A dermoscopy image of a single skin lesion · a male subject, roughly 10 years of age:
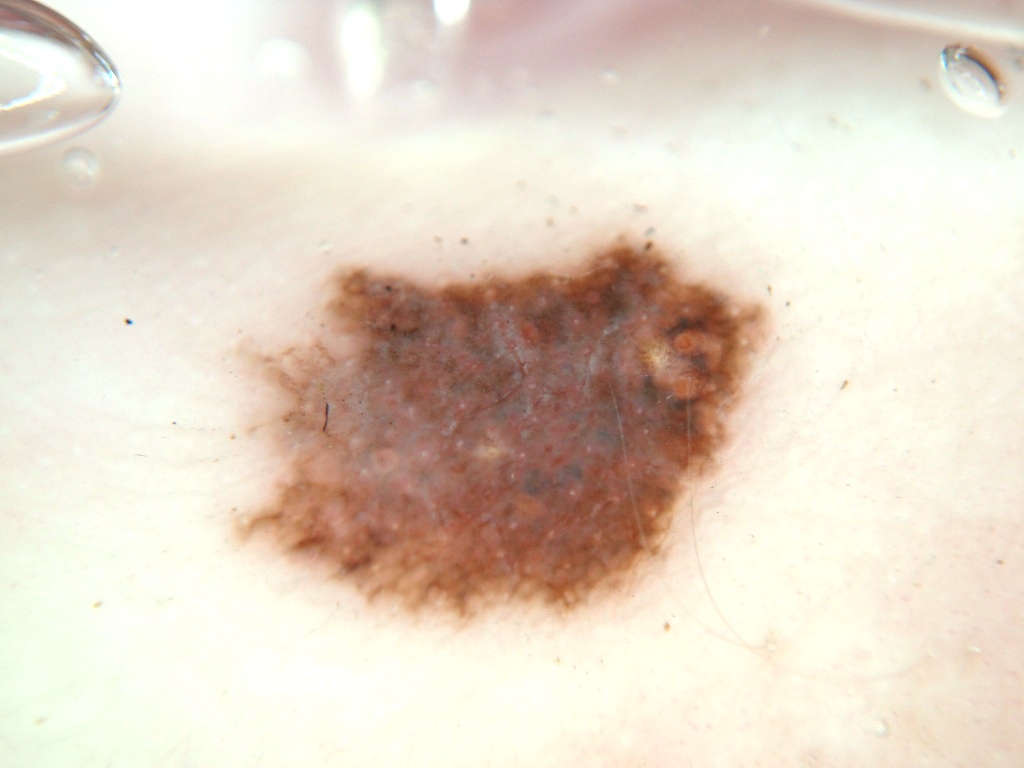features = milia-like cysts and pigment network; absent: streaks, globules, and negative network | bounding box = (170, 176, 795, 653) | diagnostic label = a melanocytic nevus, a benign skin lesion.